A skin lesion imaged with a dermatoscope. The subject is a female approximately 45 years of age:
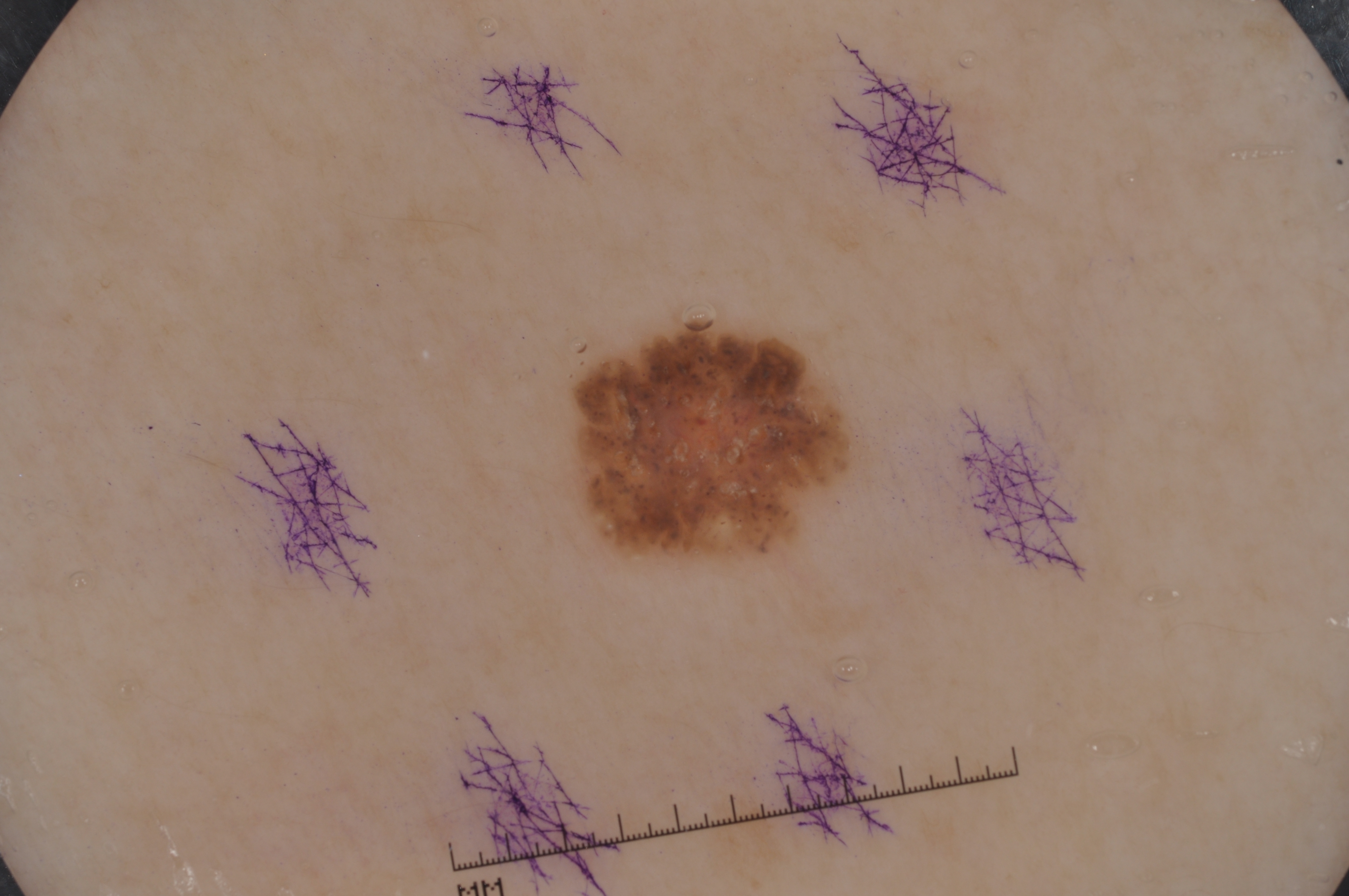location — 569, 322, 854, 560 | features — milia-like cysts; absent: streaks, negative network, and pigment network | diagnostic label — a seborrheic keratosis.